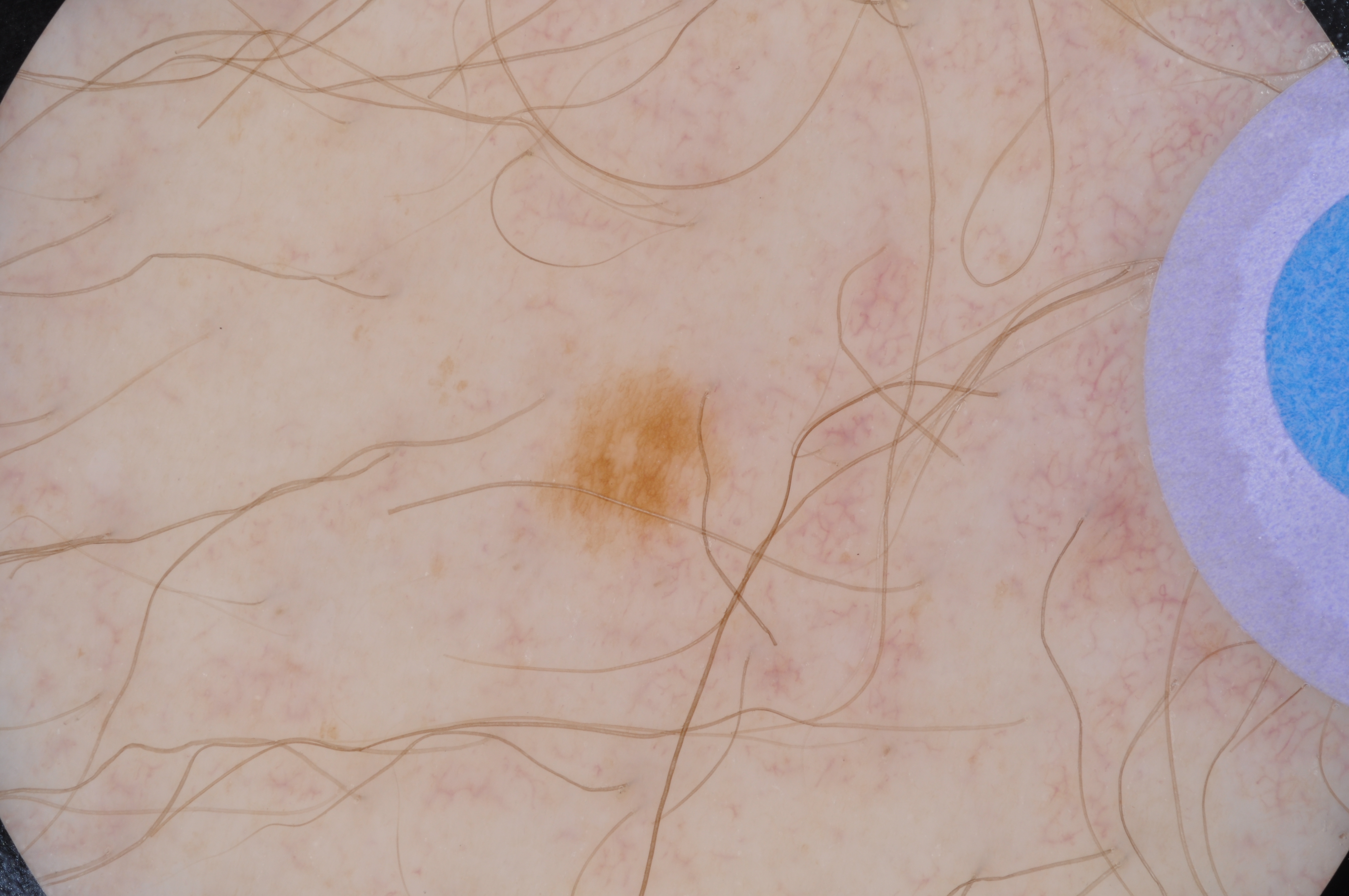image type: dermatoscopic image of a skin lesion; dermoscopic features not present: globules and streaks; location: [527,357,750,572]; diagnostic label: a benign lesion.